This is a close-up image · the lesion involves the back of the torso, back of the hand, leg, front of the torso and arm: 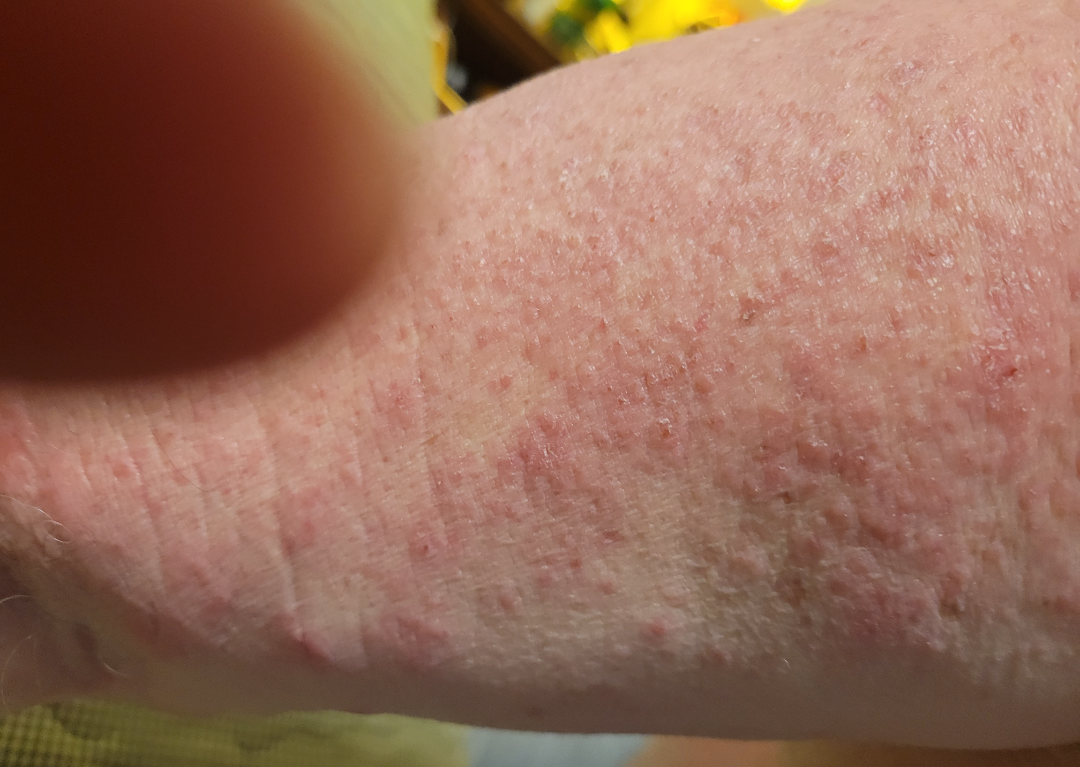| field | value |
|---|---|
| clinical impression | single-reviewer assessment: the favored diagnosis is Eczema; also raised was Scabies; possibly Allergic Contact Dermatitis |